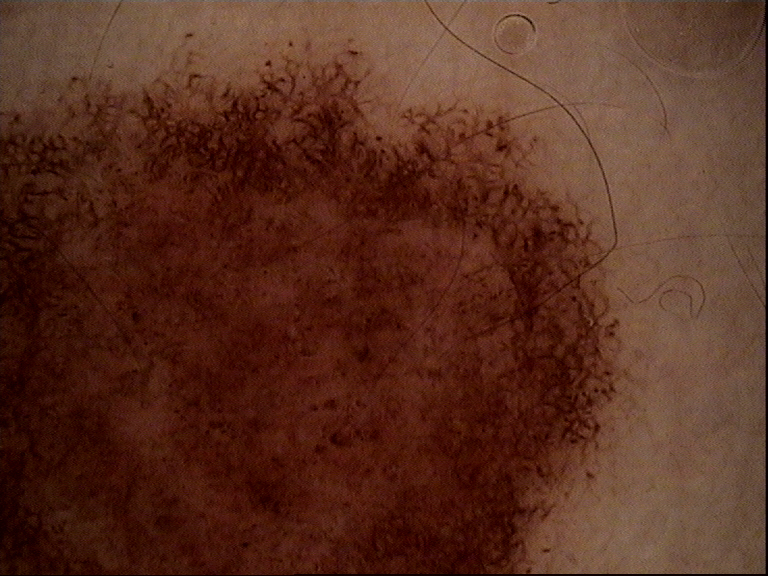diagnostic label=congenital dysplastic compound nevus (expert consensus)